A male subject aged 83; referred with a clinical suspicion of Bowen's disease; the patient says their skin reddens with sun exposure; a dermoscopic image of a skin lesion.
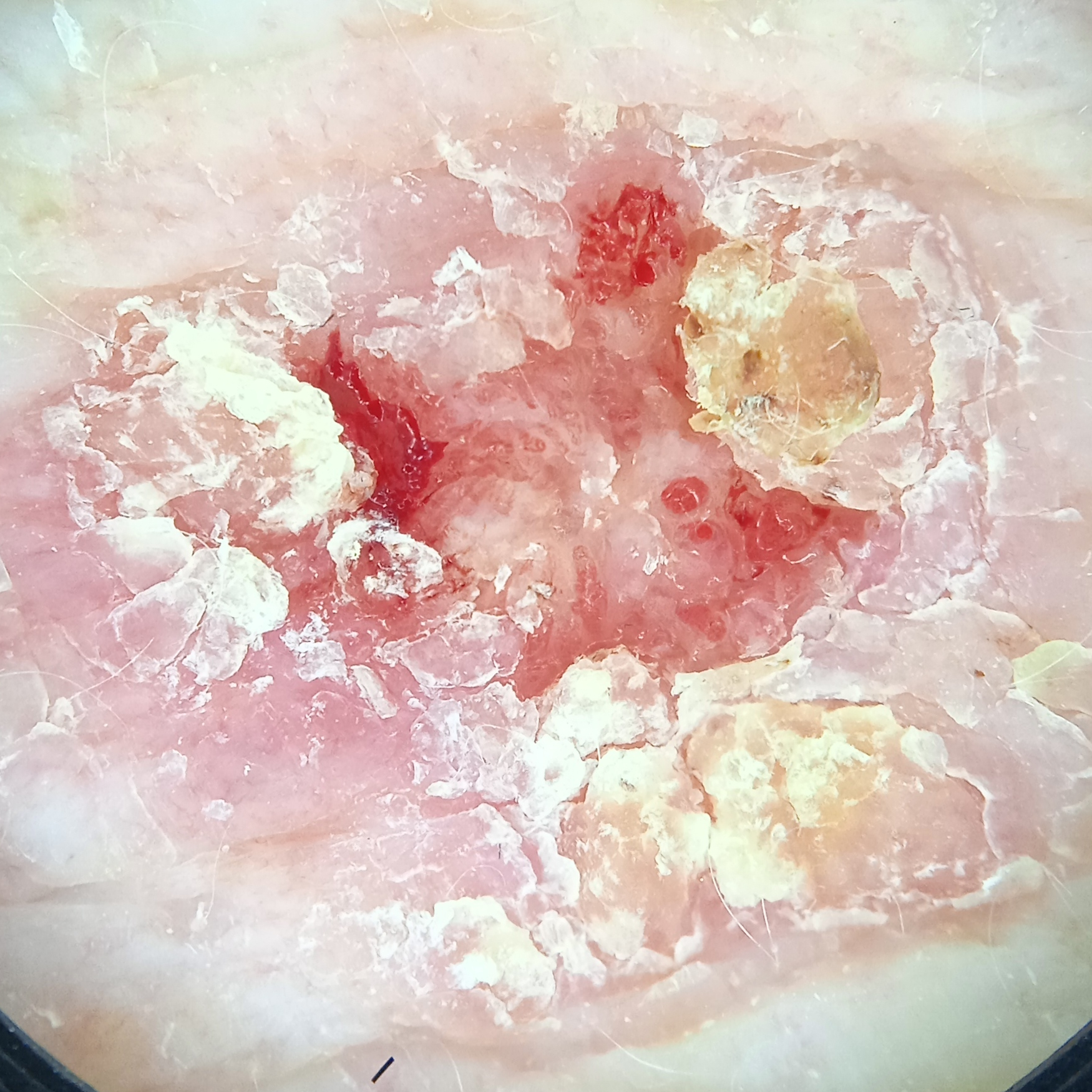Located on the torso. Measuring roughly 14.5 mm. The diagnostic impression was a squamous cell carcinoma.